A dermoscopy image of a single skin lesion:
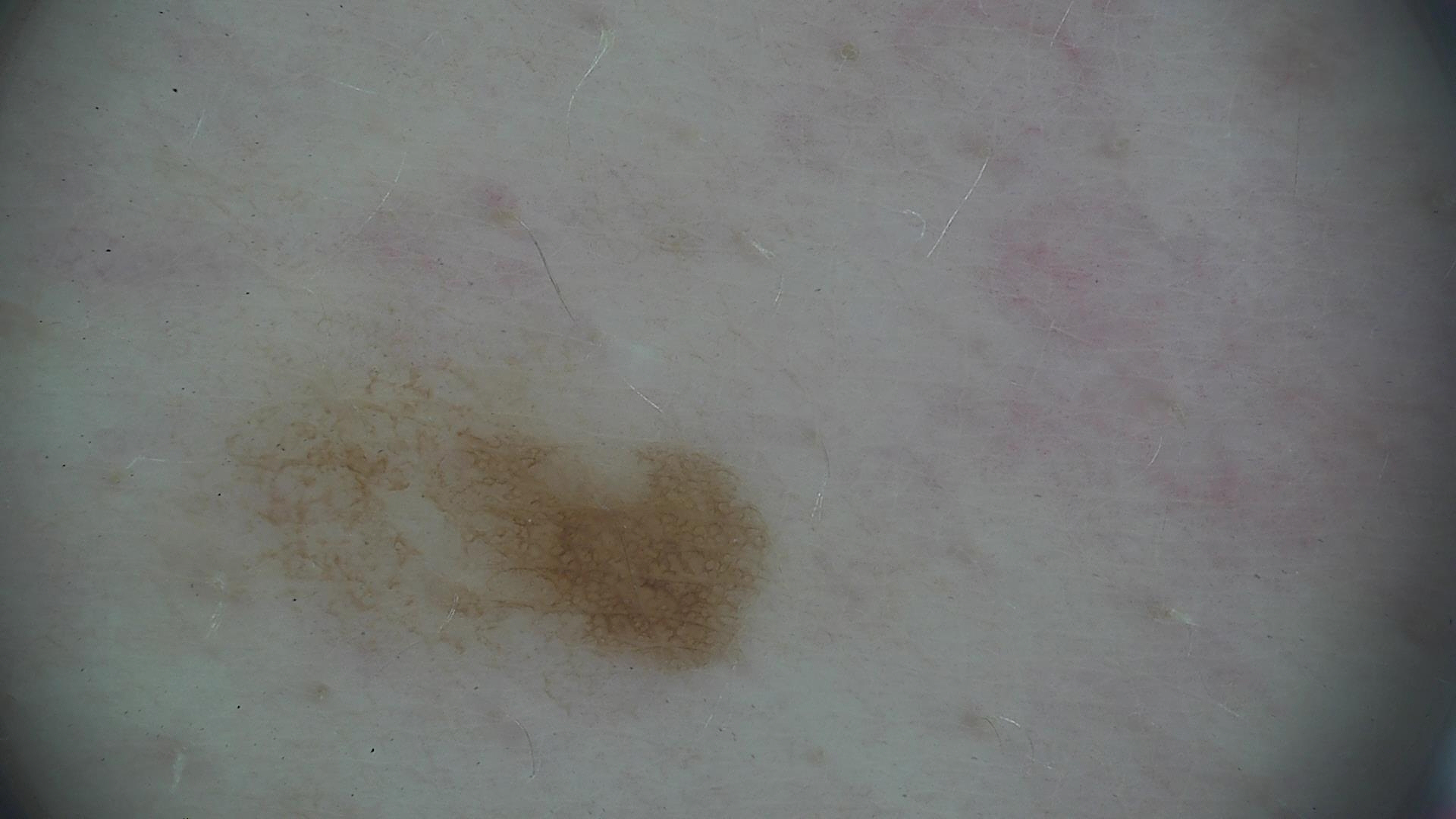Conclusion:
Diagnosed as a dysplastic junctional nevus.